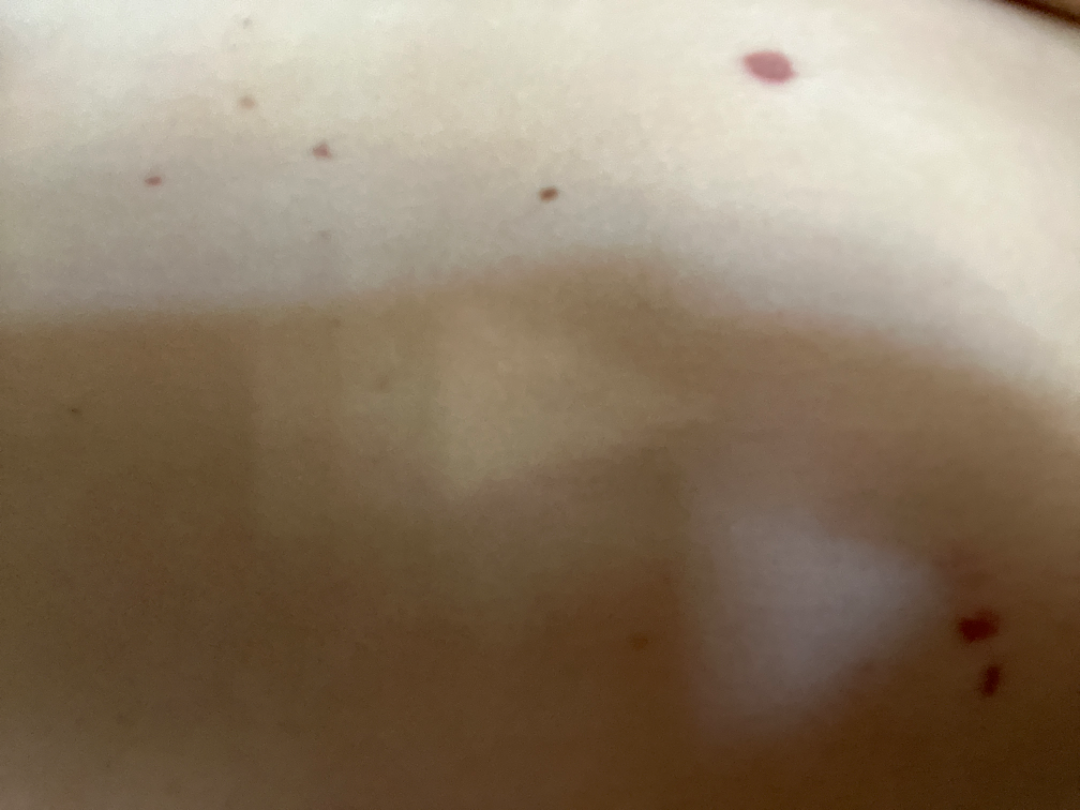The image was not sufficient for the reviewer to characterize the skin condition.
The lesion is associated with bothersome appearance.
The lesion is described as flat.
No associated systemic symptoms reported.
Present for less than one week.
A close-up photograph.
The lesion involves the front of the torso.